Imaged for a research study, with no referral diagnosis recorded · a female subject age 73 · a clinical close-up of a skin lesion:
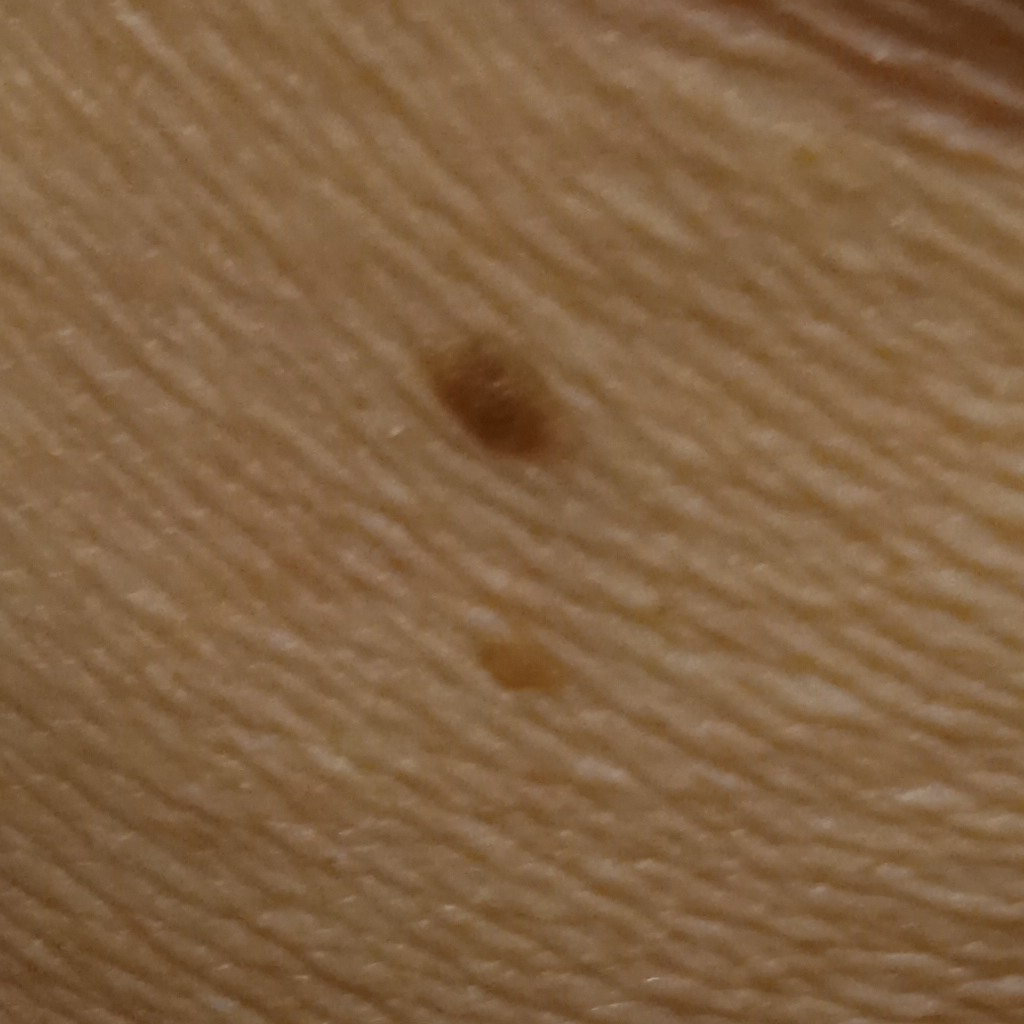<record>
<lesion_location>the back</lesion_location>
<lesion_size>
<diameter_mm>6.0</diameter_mm>
</lesion_size>
<diagnosis>
<name>seborrheic keratosis</name>
<malignancy>benign</malignancy>
</diagnosis>
</record>